The patient says their skin reddens with sun exposure. Collected as part of a research study, without a referral diagnosis. A macroscopic clinical photograph of a skin lesion. The patient describes having a moderate number of moles. A female patient aged 59 — 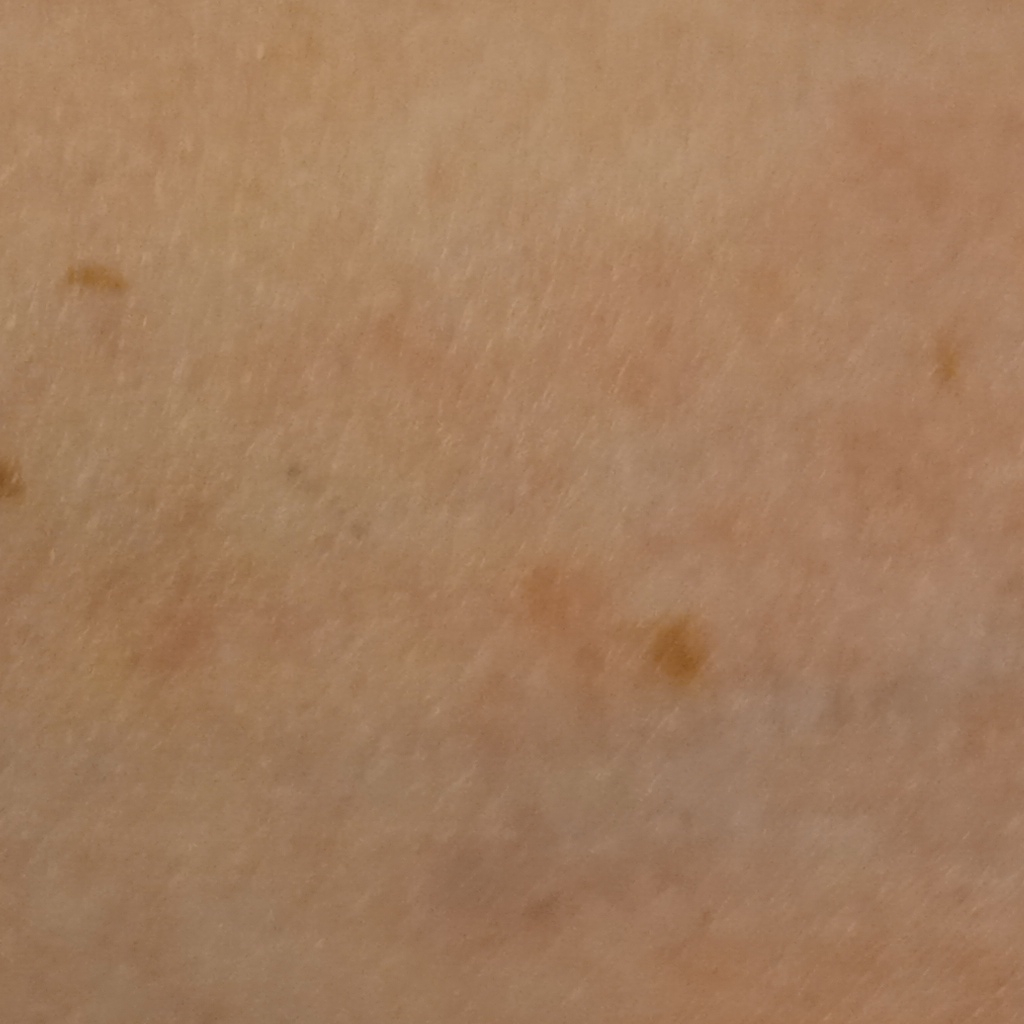Q: Where is the lesion?
A: an arm
Q: How large is the lesion?
A: 6.5 mm
Q: What was the diagnosis?
A: melanocytic nevus (dermatologist consensus)